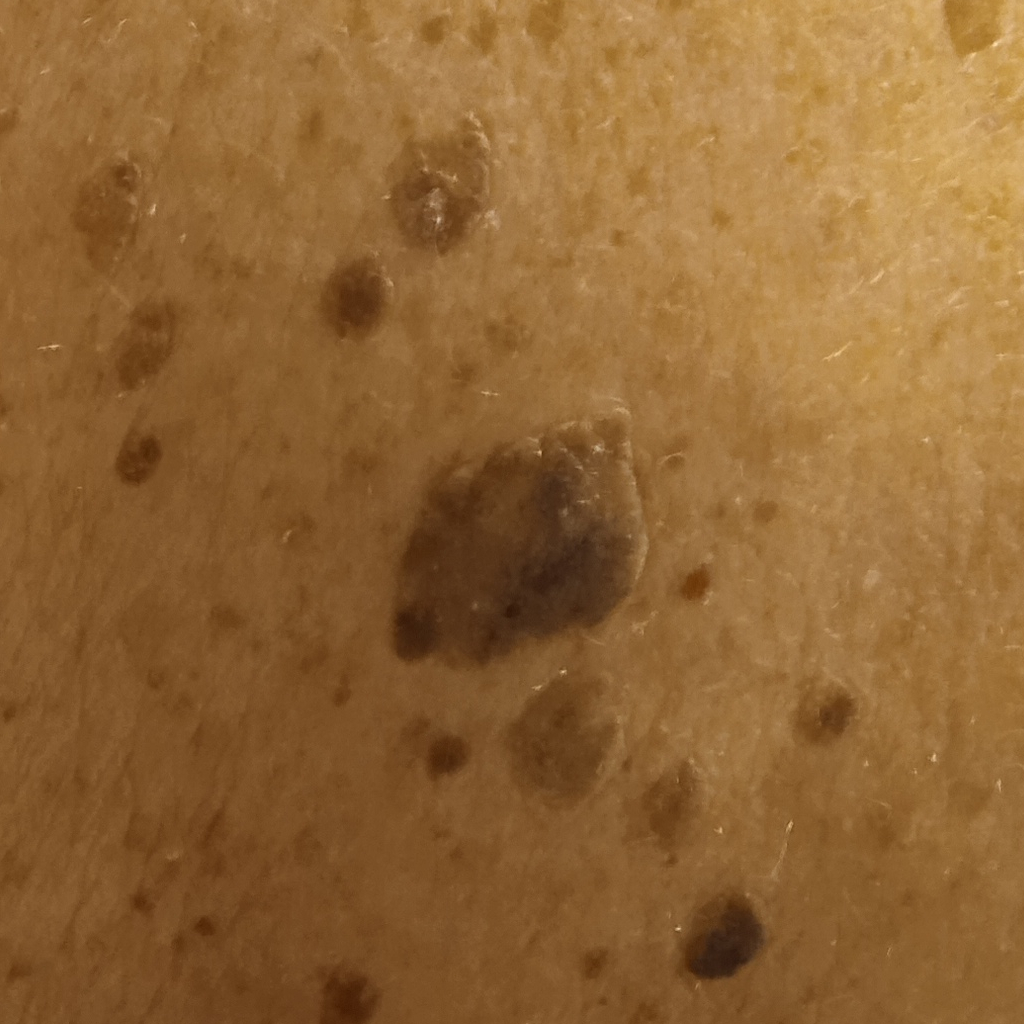A macroscopic clinical photograph of a skin lesion. Imaged for a research study, with no referral diagnosis recorded. A female patient 78 years of age. The patient says their skin tans without first burning. The patient describes having numerous moles. The lesion is on the back. Measuring roughly 15.7 mm. Dermatologist review favored a seborrheic keratosis.